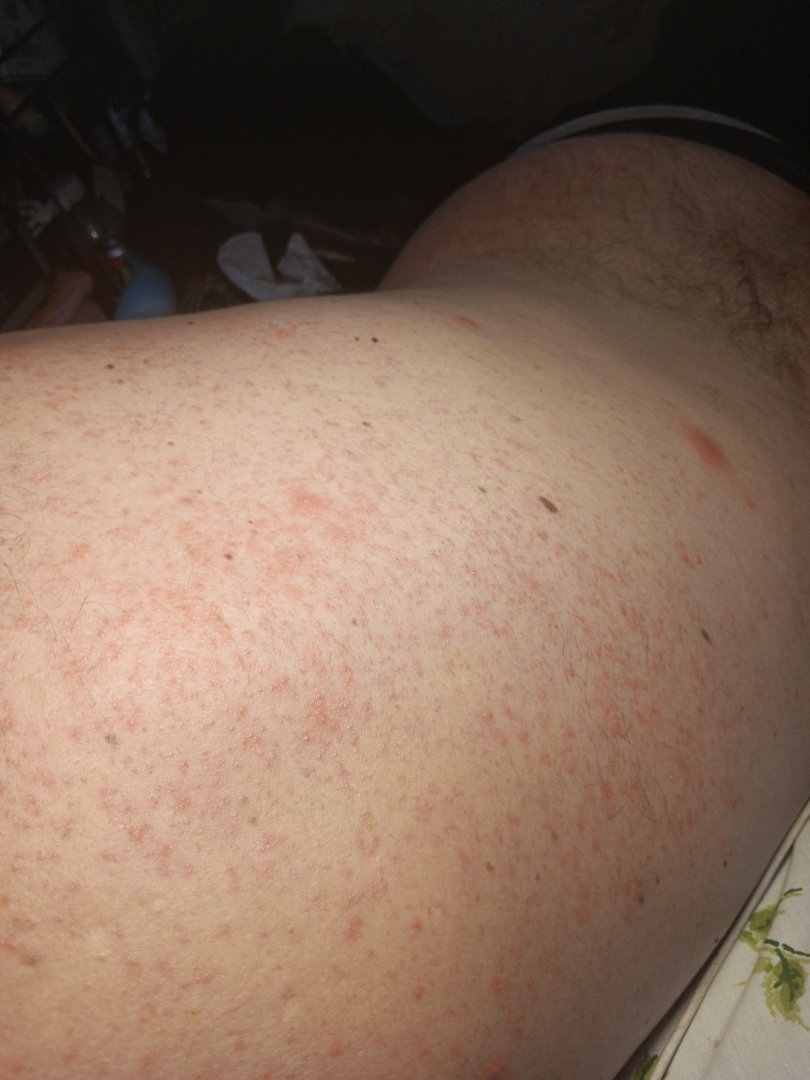{"symptoms": "itching", "texture": "raised or bumpy", "shot_type": "at an angle", "systemic_symptoms": "none reported", "body_site": "back of the torso", "patient_category": "a rash", "duration": "less than one week", "differential": {"leading": ["Acute dermatitis, NOS"]}}